The arm is involved · male contributor, age 30–39 · this image was taken at a distance: 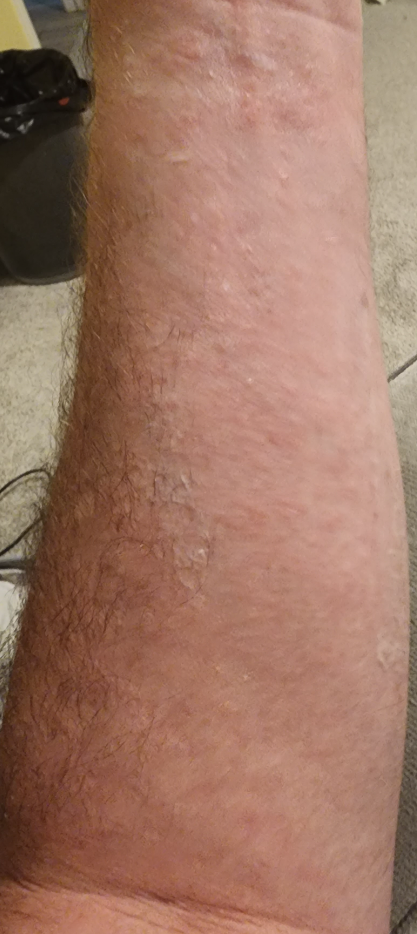The lesion is associated with bothersome appearance and itching. No relevant systemic symptoms. The contributor notes the lesion is raised or bumpy. The patient considered this a rash. Present for about one day. On teledermatology review: Eczema (leading); Allergic Contact Dermatitis (possible); Viral Exanthem (unlikely); Drug Rash (unlikely).